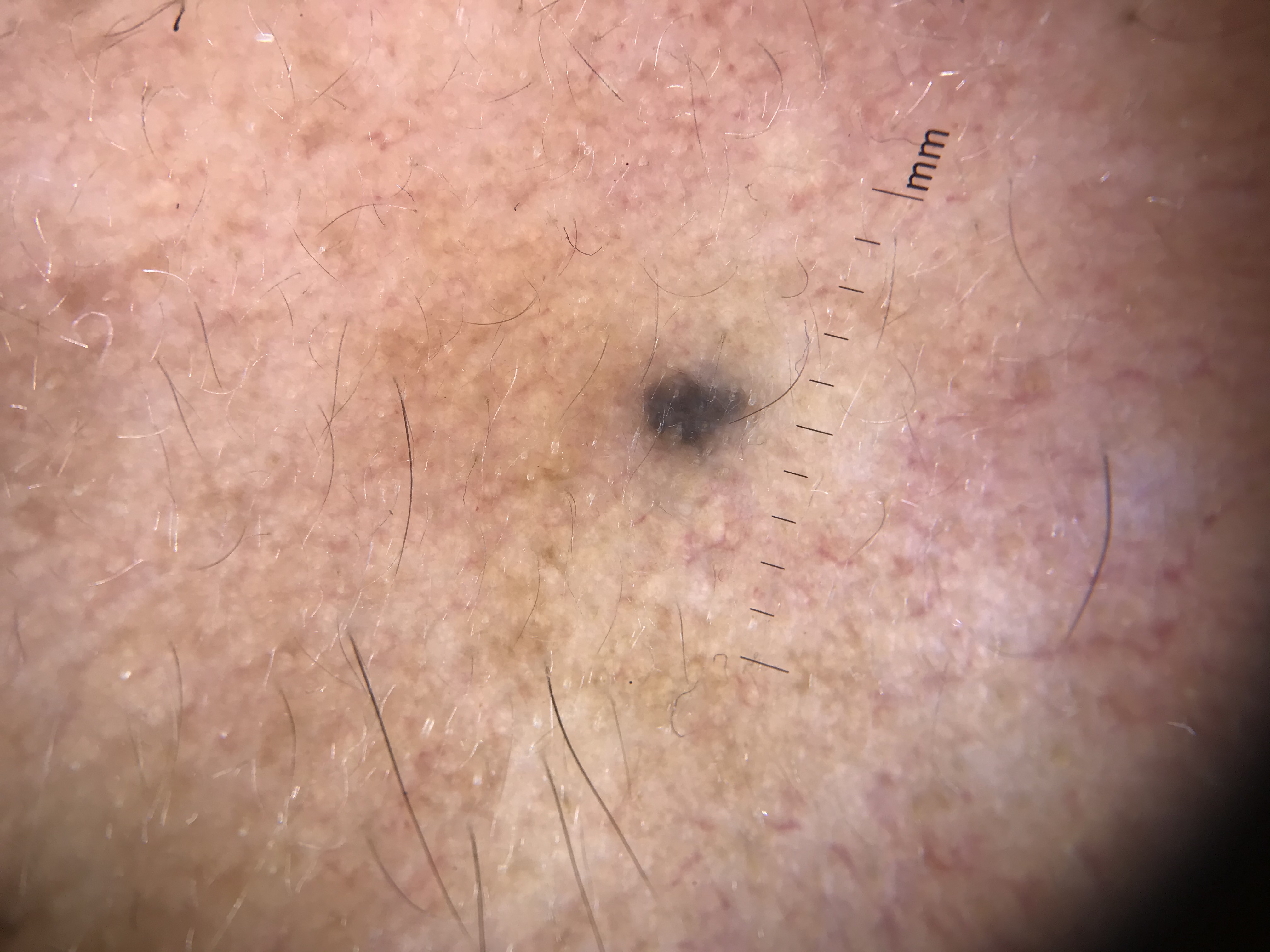Diagnosed as a blue nevus.